The photograph is a close-up of the affected area. The lesion involves the arm — 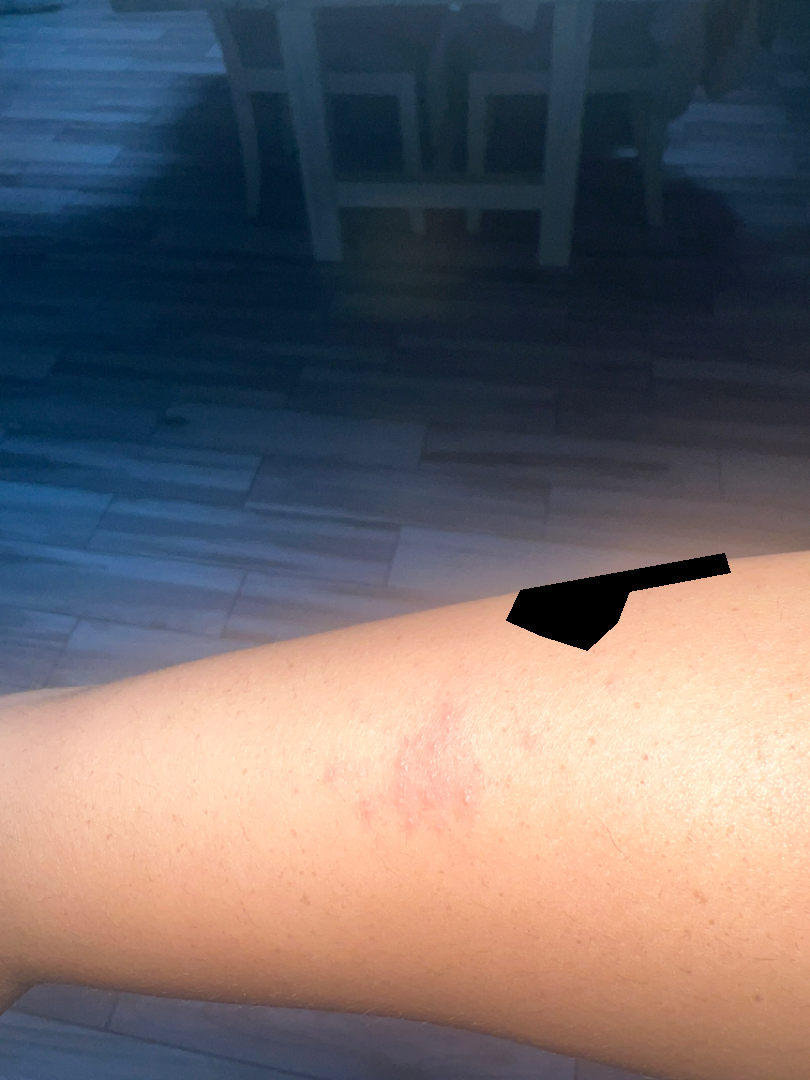Q: Could the case be diagnosed?
A: unable to determine